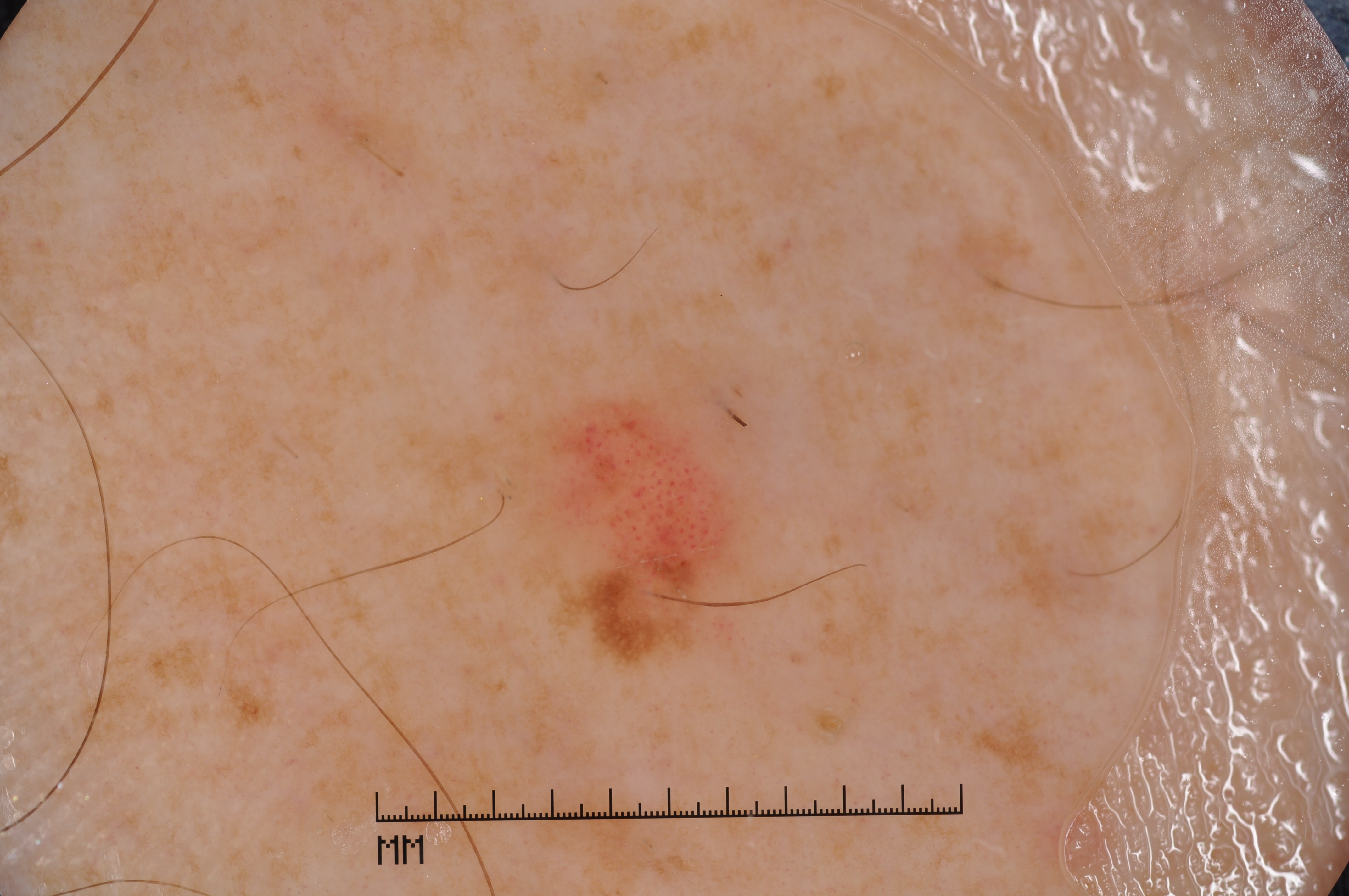A skin lesion imaged with a dermatoscope. The lesion takes up about 4% of the image. Dermoscopically, the lesion shows pigment network and milia-like cysts; no negative network or streaks. As (left, top, right, bottom), lesion location: bbox(527, 378, 759, 644). The lesion was assessed as a melanocytic nevus, a benign skin lesion.